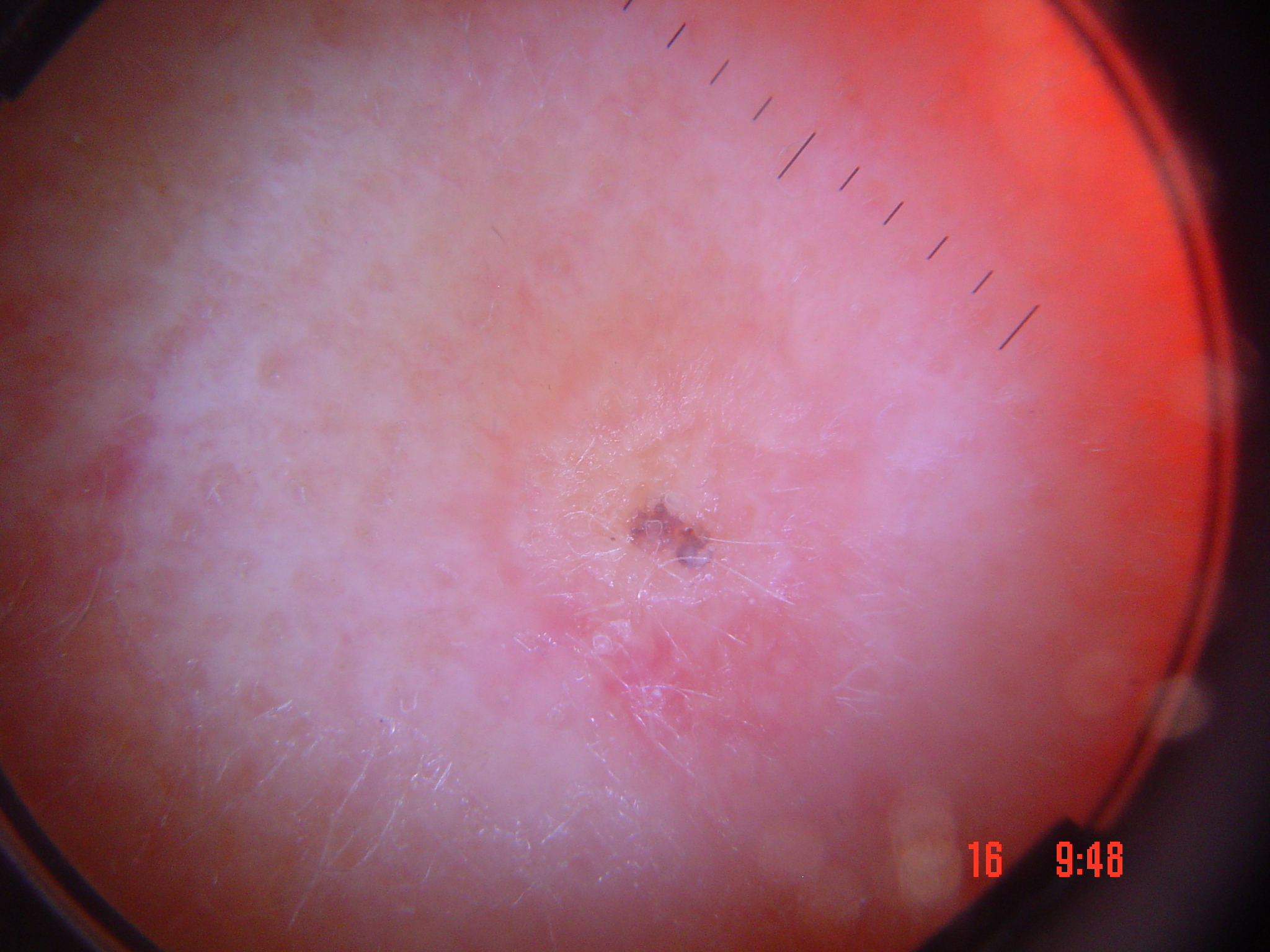Summary: A skin lesion imaged with a dermatoscope. Pathology: Biopsy-confirmed as a malignant, keratinocytic lesion — a squamous cell carcinoma.